Close-up view:
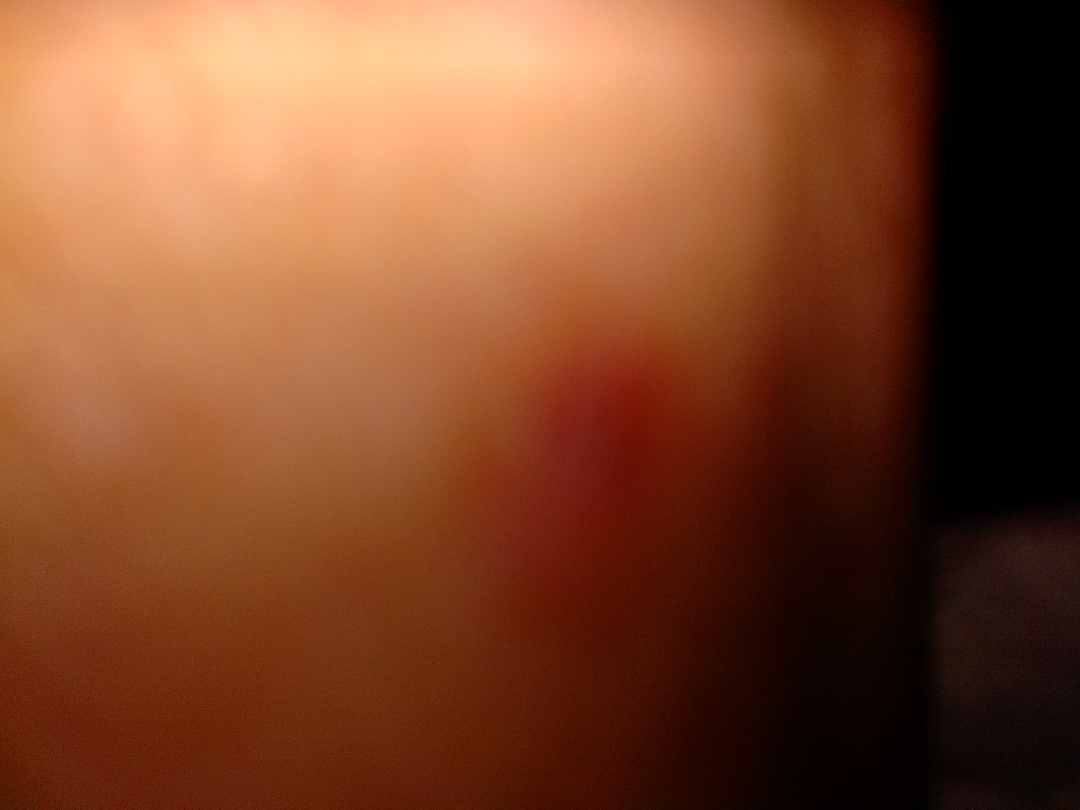Most consistent with Insect Bite.